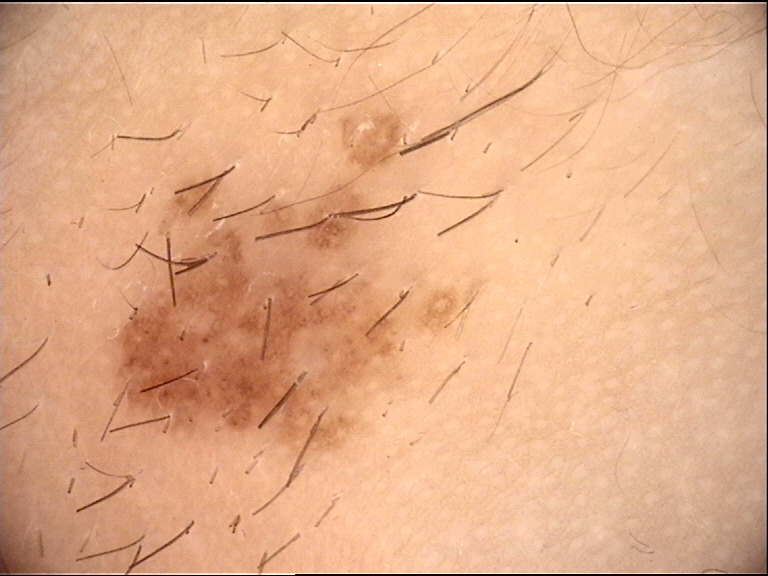A dermoscopic image of a skin lesion. Diagnosed as a banal lesion — a congenital compound nevus.